A skin lesion imaged with a dermatoscope:
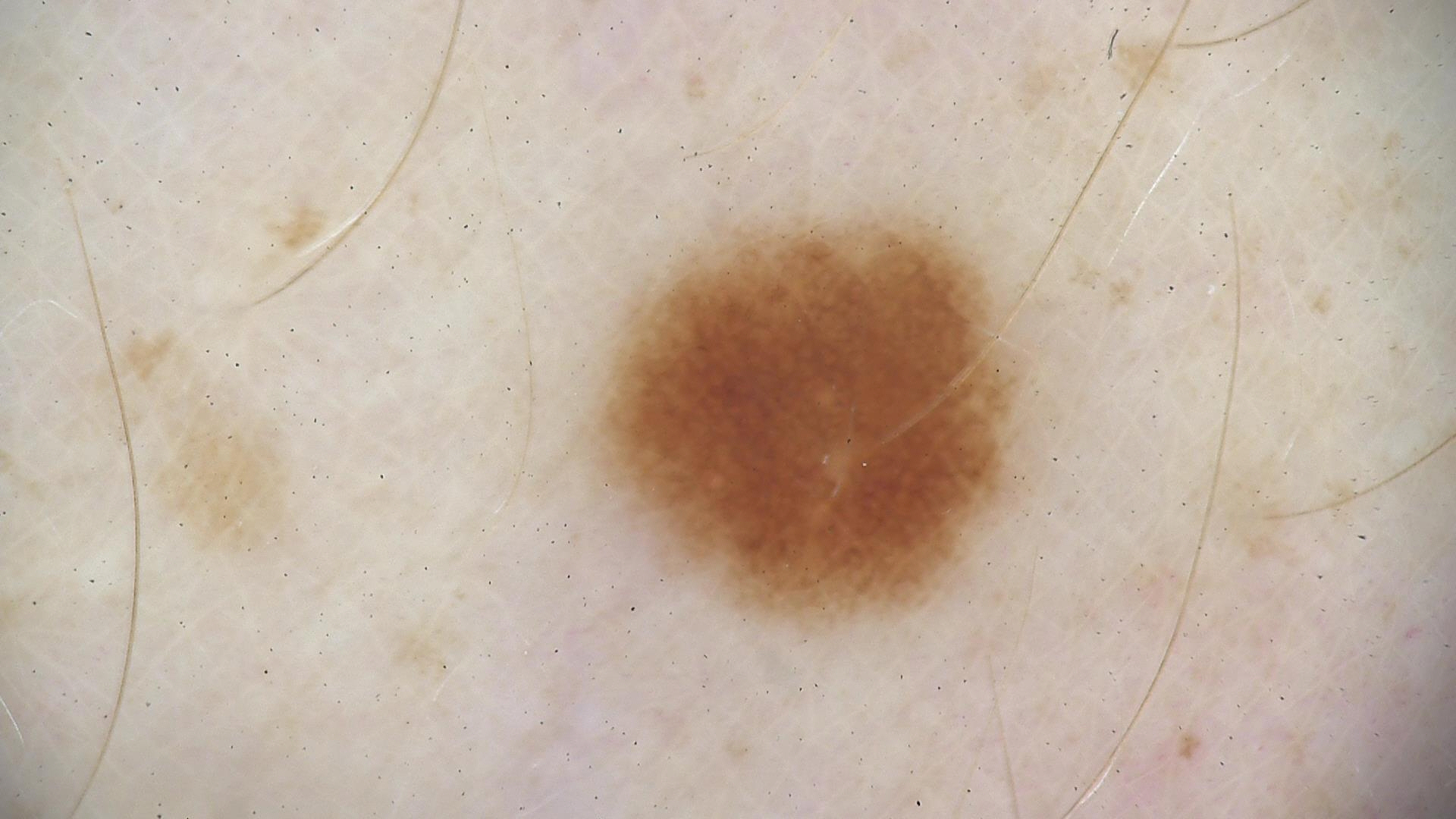assessment: dysplastic junctional nevus (expert consensus).